A female patient 92 years old. Acquired for a research image collection, with no referral diagnosis: 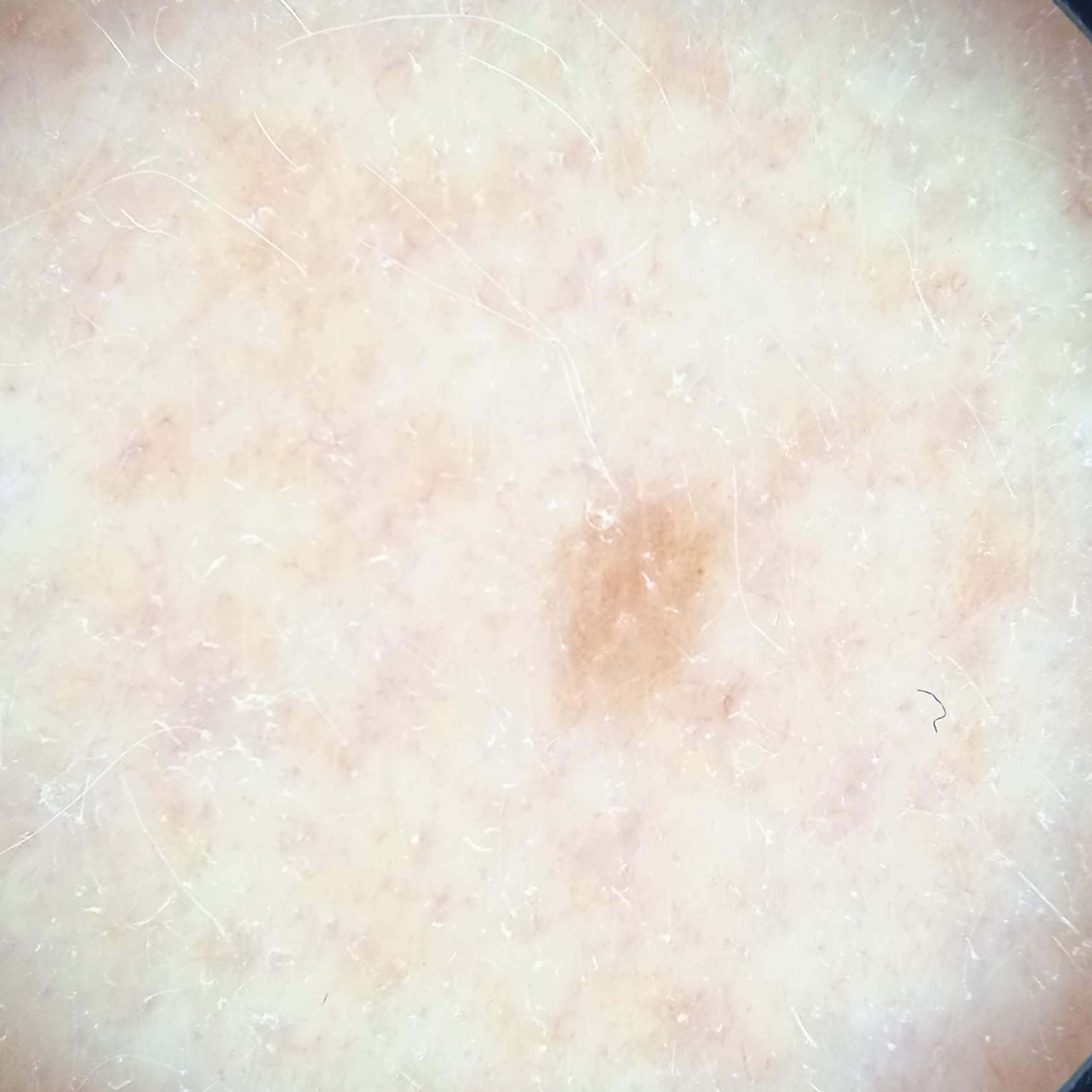Findings:
– size · 2.9 mm
– diagnosis · melanocytic nevus (dermatologist consensus)